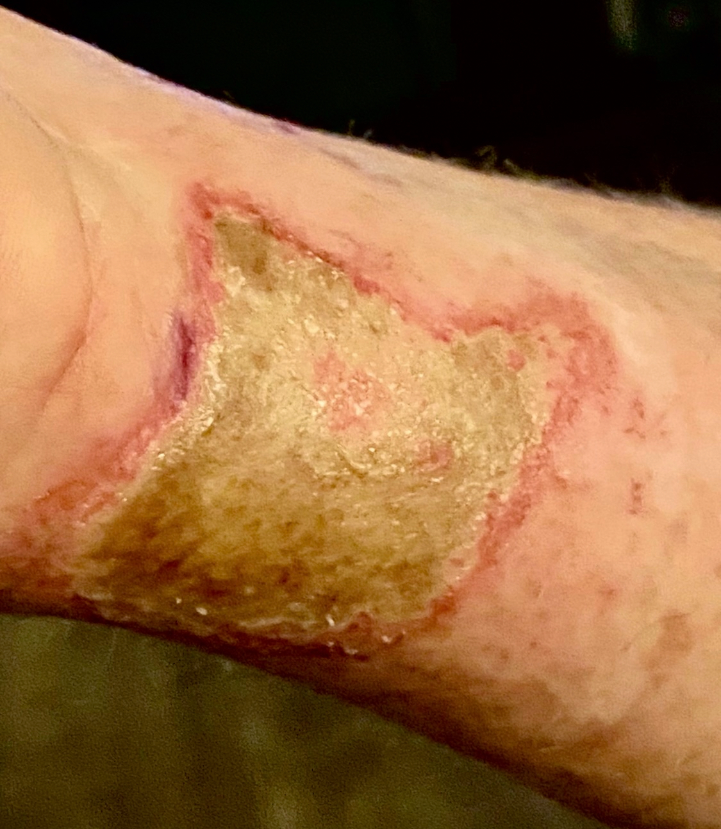assessment = indeterminate
onset = less than one week
contributor = male, age 60–69
skin tone = Fitzpatrick skin type II
symptoms = bothersome appearance, enlargement, burning, bleeding and pain
lesion texture = raised or bumpy
self-categorized as = a growth or mole
shot type = close-up